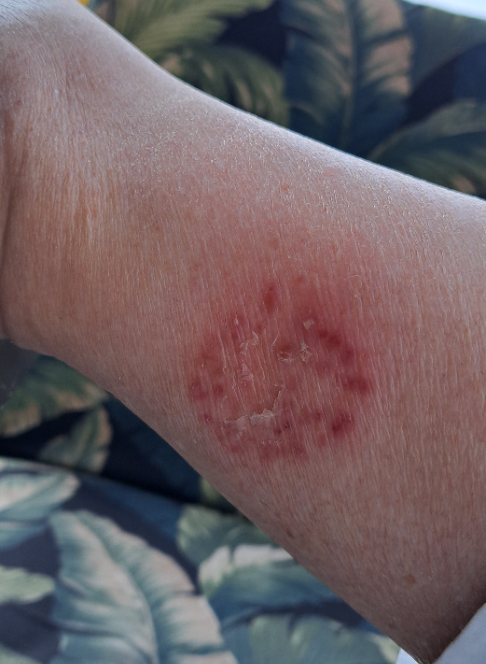Patient information: Reported duration is one to four weeks. Female subject, age 70–79. This image was taken at an angle. The contributor notes bothersome appearance. Skin tone: Fitzpatrick phototype II. Texture is reported as raised or bumpy. The patient reported no systemic symptoms. The lesion involves the leg. Self-categorized by the patient as a rash. Review: On dermatologist assessment of the image: consistent with Eczema.